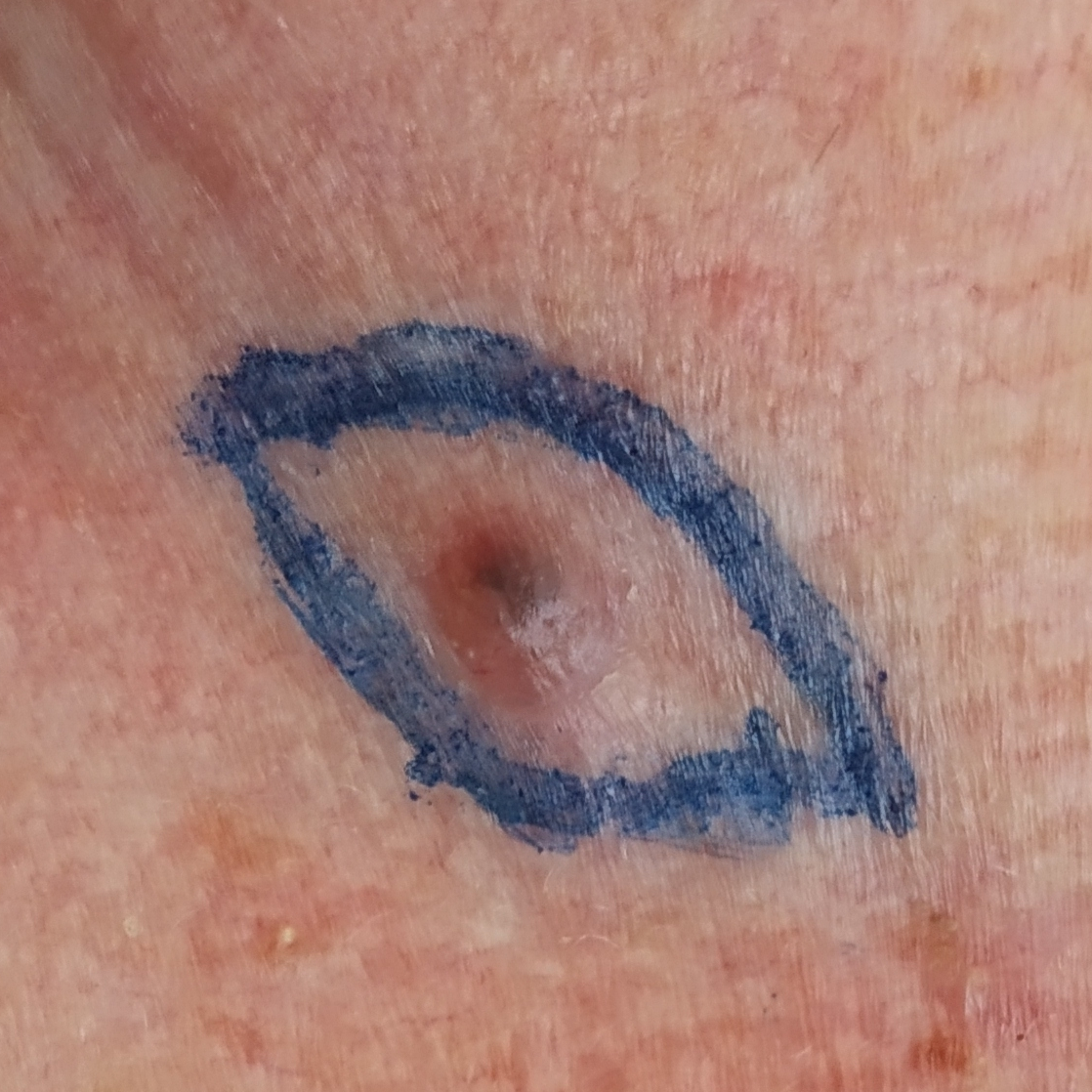Findings: The patient is FST II. A male subject in their 60s. History notes prior malignancy (patient or family). A clinical photograph of a skin lesion. The lesion is located on an ear. The lesion is roughly 8 by 5 mm. Per patient report, the lesion is elevated and itches. Conclusion: Confirmed on histopathology as a basal cell carcinoma.